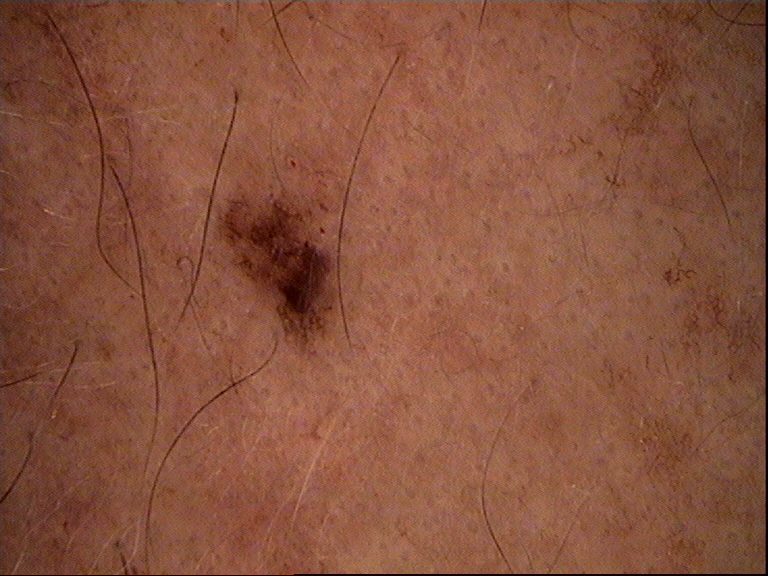diagnosis = dysplastic junctional nevus (expert consensus).